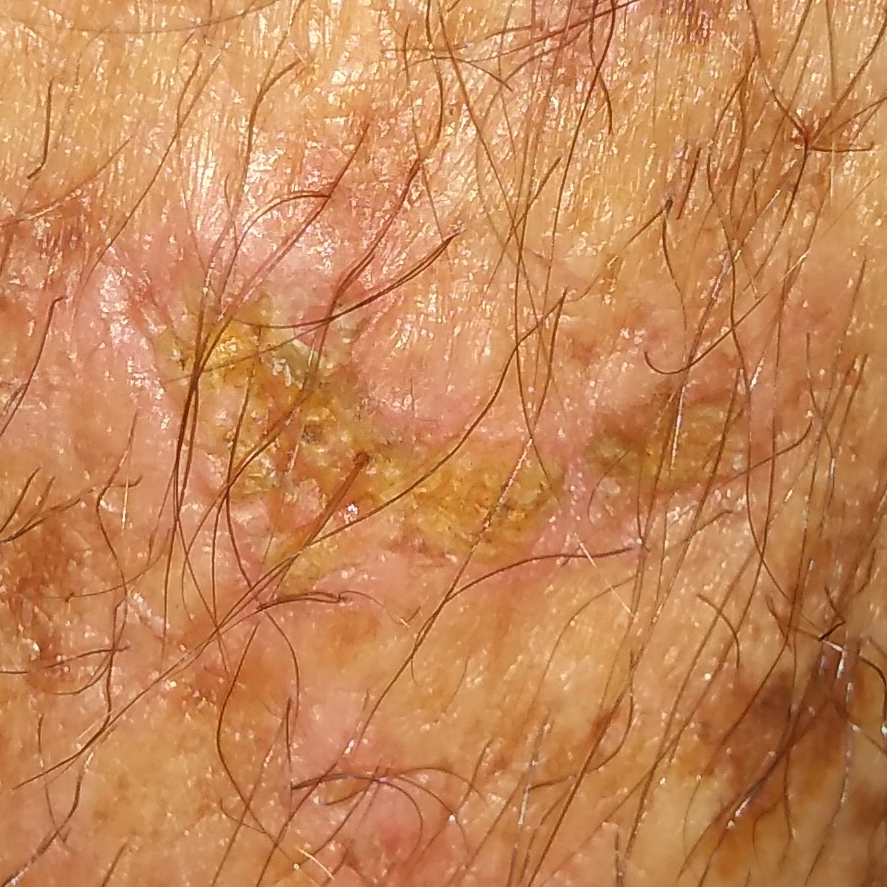image type=smartphone clinical photo; exposure history=pesticide exposure, prior skin cancer (patient or family), prior malignancy (patient or family), no alcohol use; subject=female, in their mid-60s; FST=II; site=a forearm; size=approx. 16 × 8 mm; symptoms=change in appearance, growth, itching / no bleeding; pathology=actinic keratosis (biopsy-proven).